A dermoscopic photograph of a skin lesion:
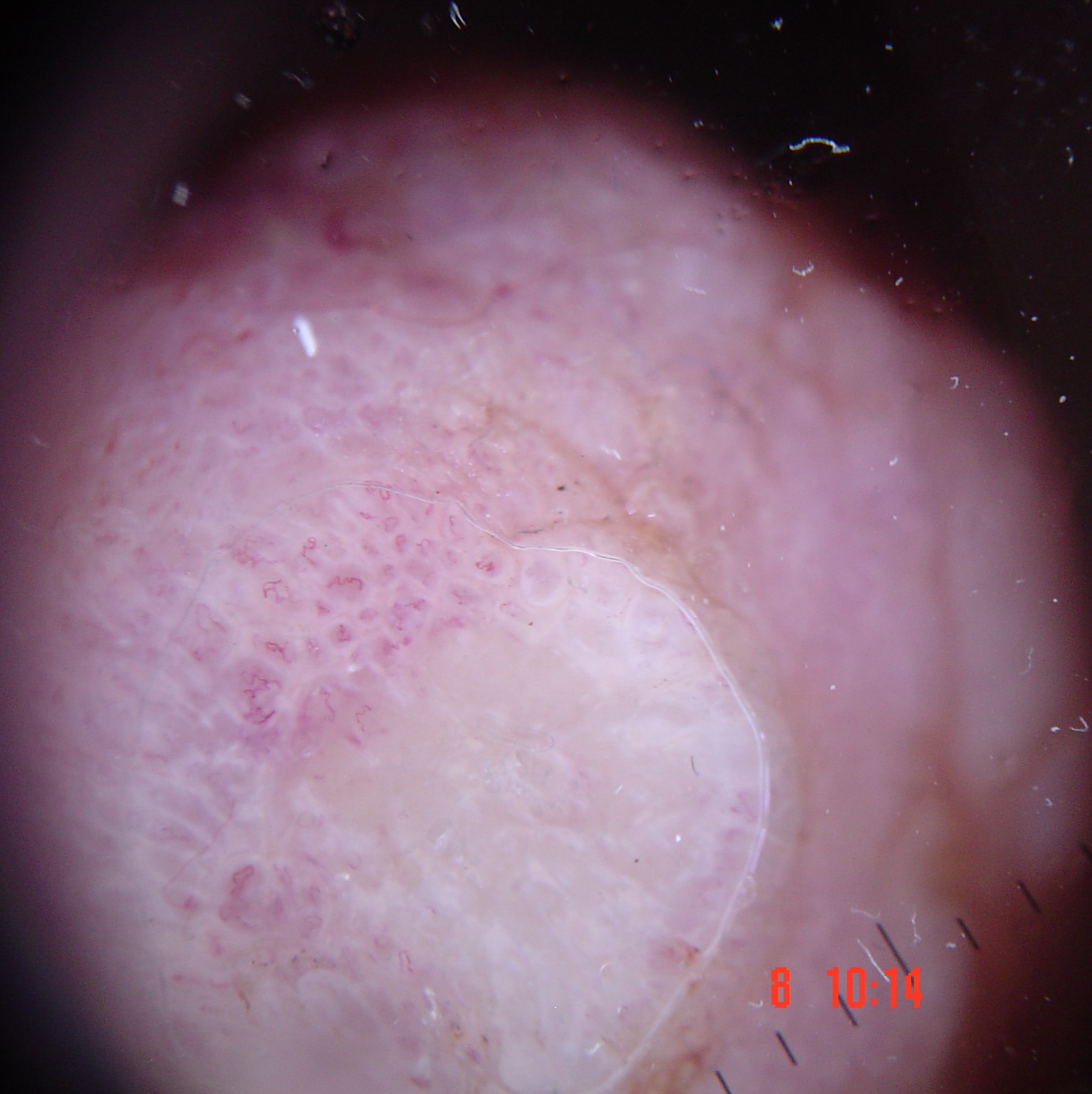Biopsy-confirmed as an acral nodular melanoma.